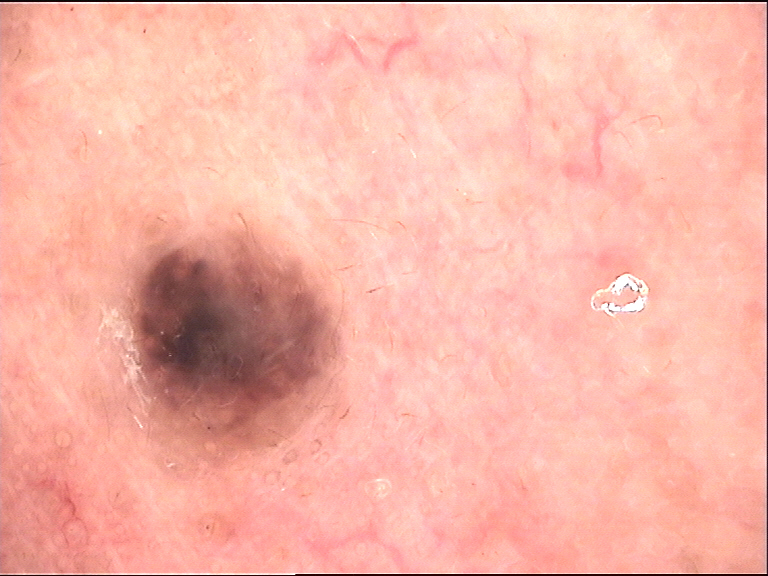A dermoscopic image of a skin lesion. The morphology is that of a dermal, banal lesion. Labeled as a blue nevus.